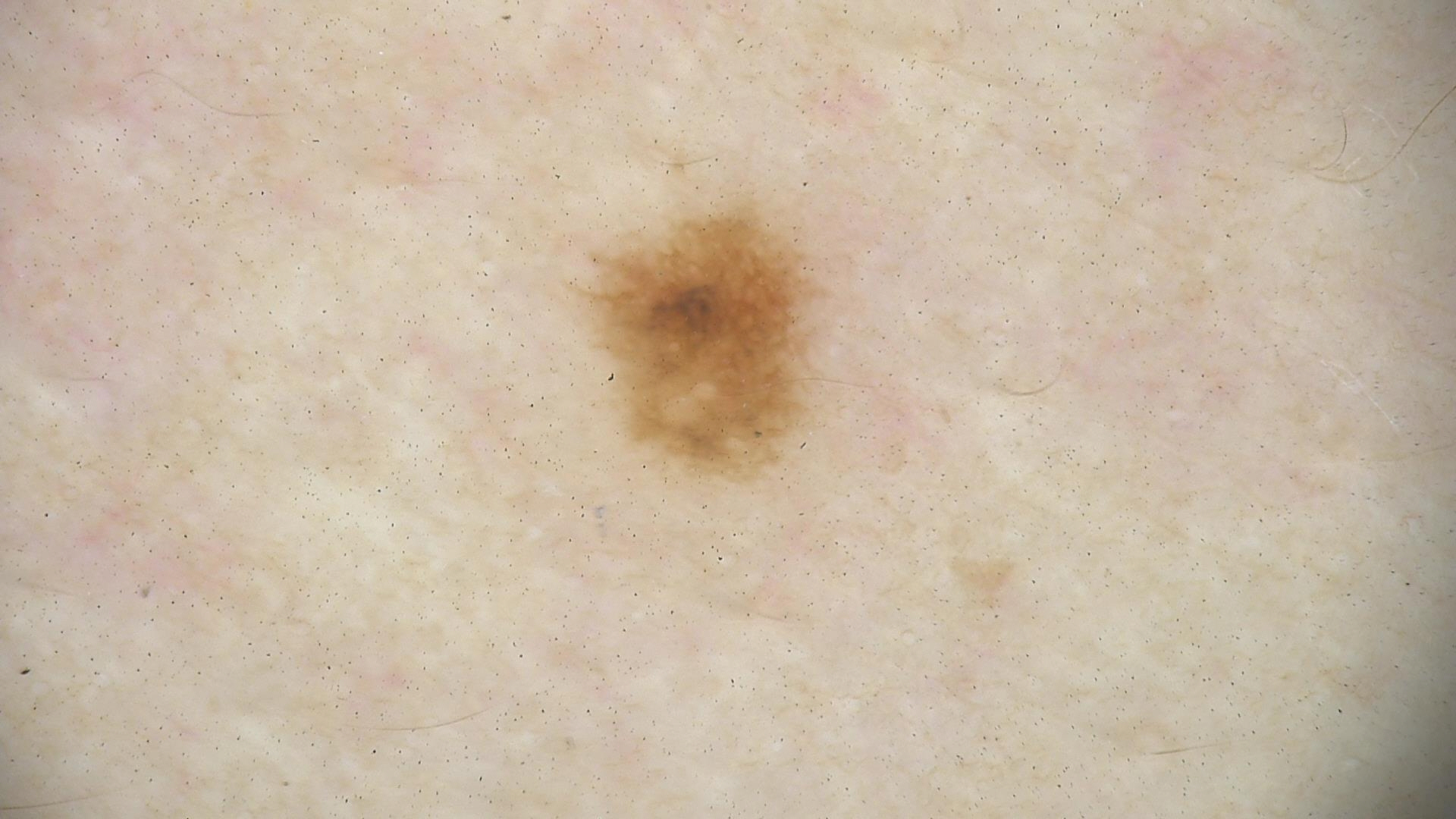The diagnosis was a benign lesion — a dysplastic junctional nevus.